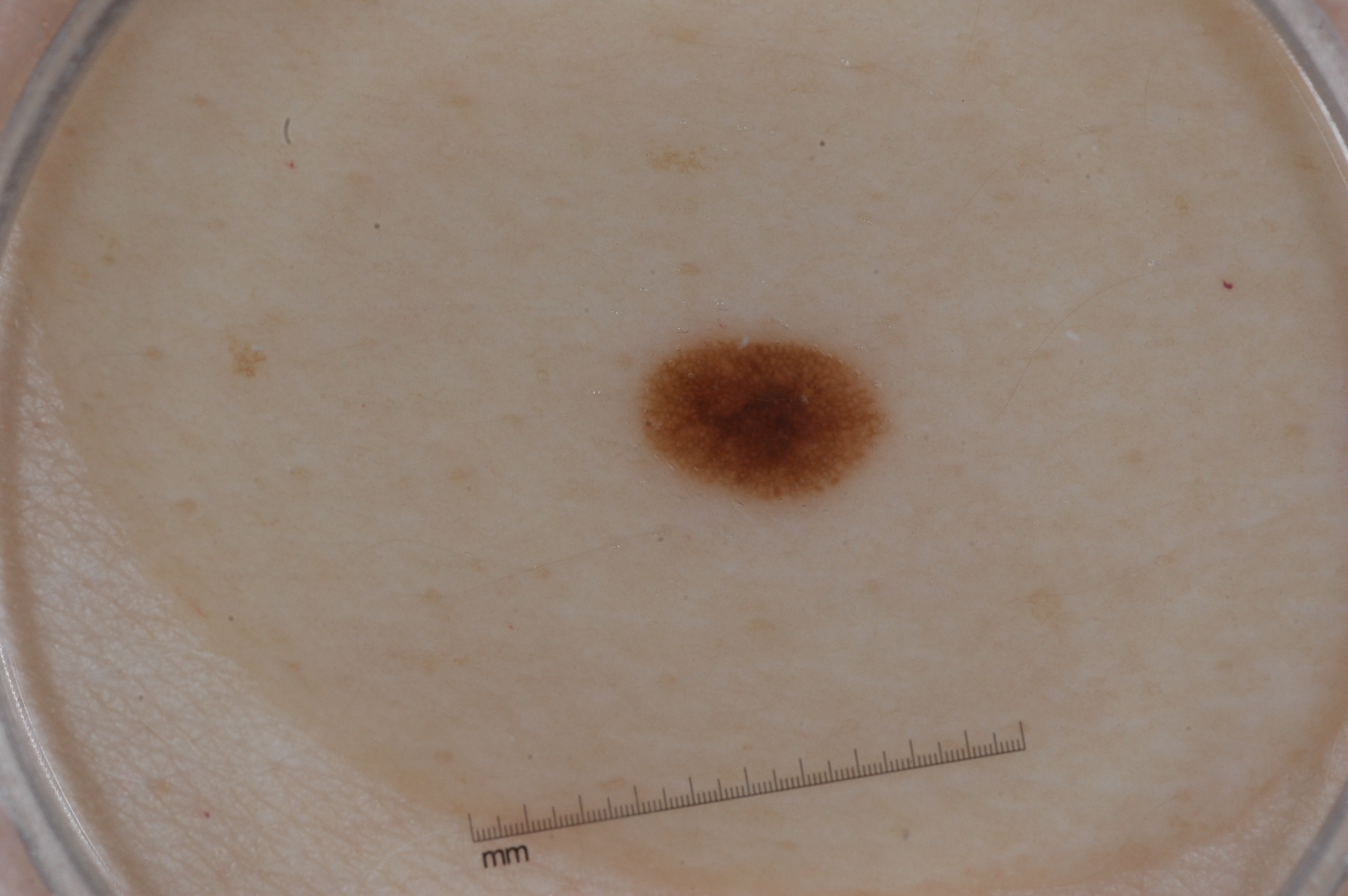patient = male, in their mid- to late 30s | image = dermoscopy | dermoscopic features = pigment network | lesion bbox = bbox(643, 329, 885, 504) | diagnosis = a melanocytic nevus, a benign lesion.